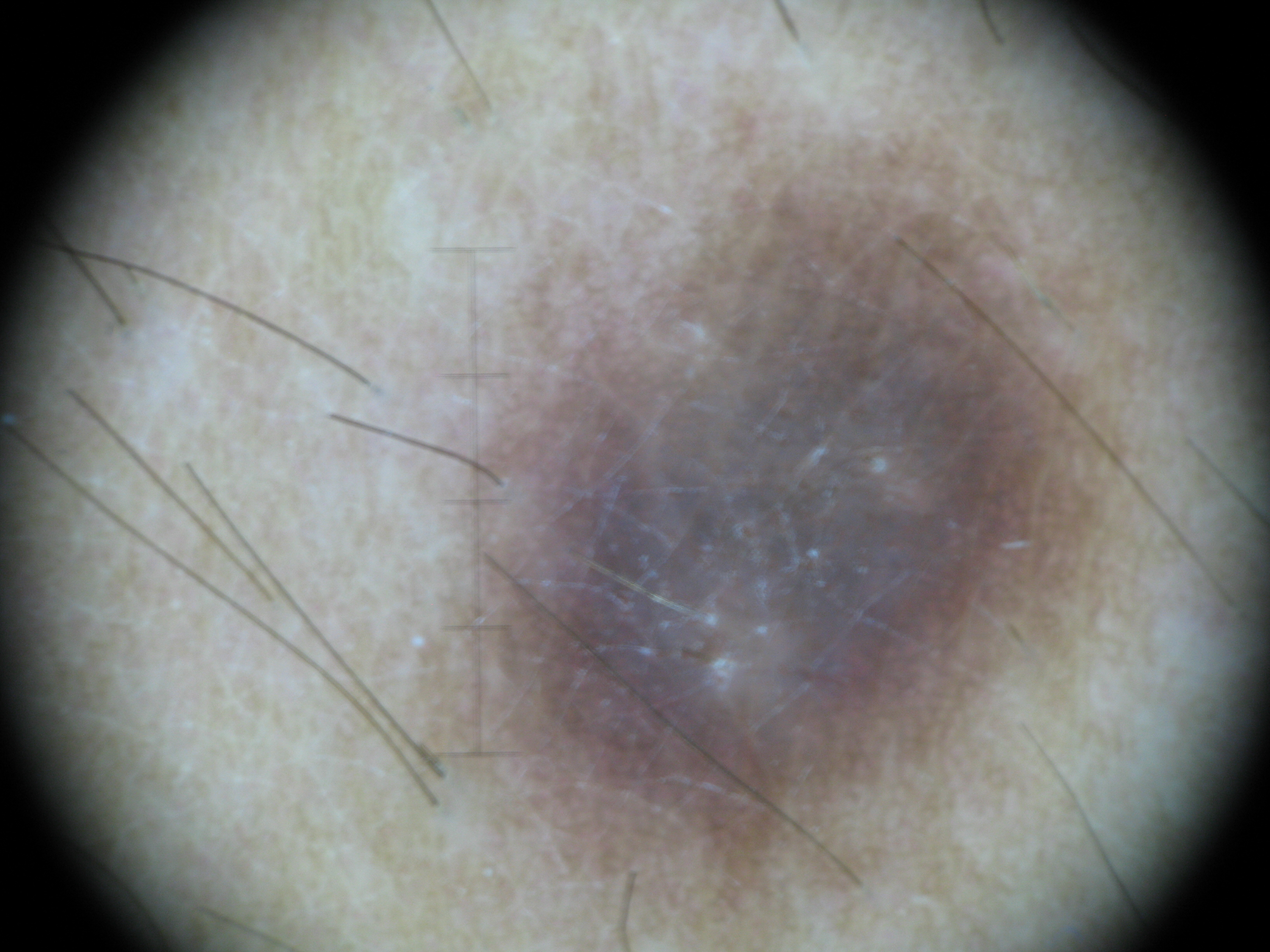Case:
Dermoscopy of a skin lesion. The architecture is that of a fibro-histiocytic lesion.
Conclusion:
The diagnosis was a benign lesion — a dermatofibroma.